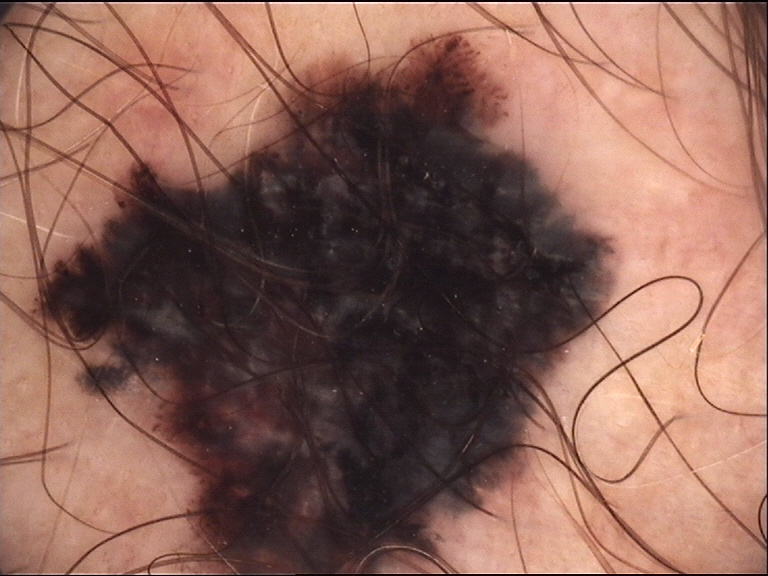Biopsy-confirmed as a melanoma.